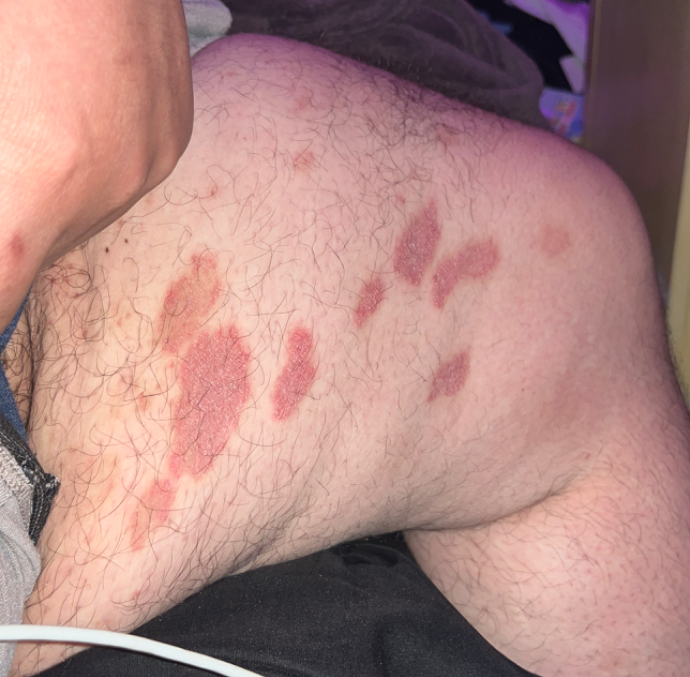differential = Psoriasis (leading).